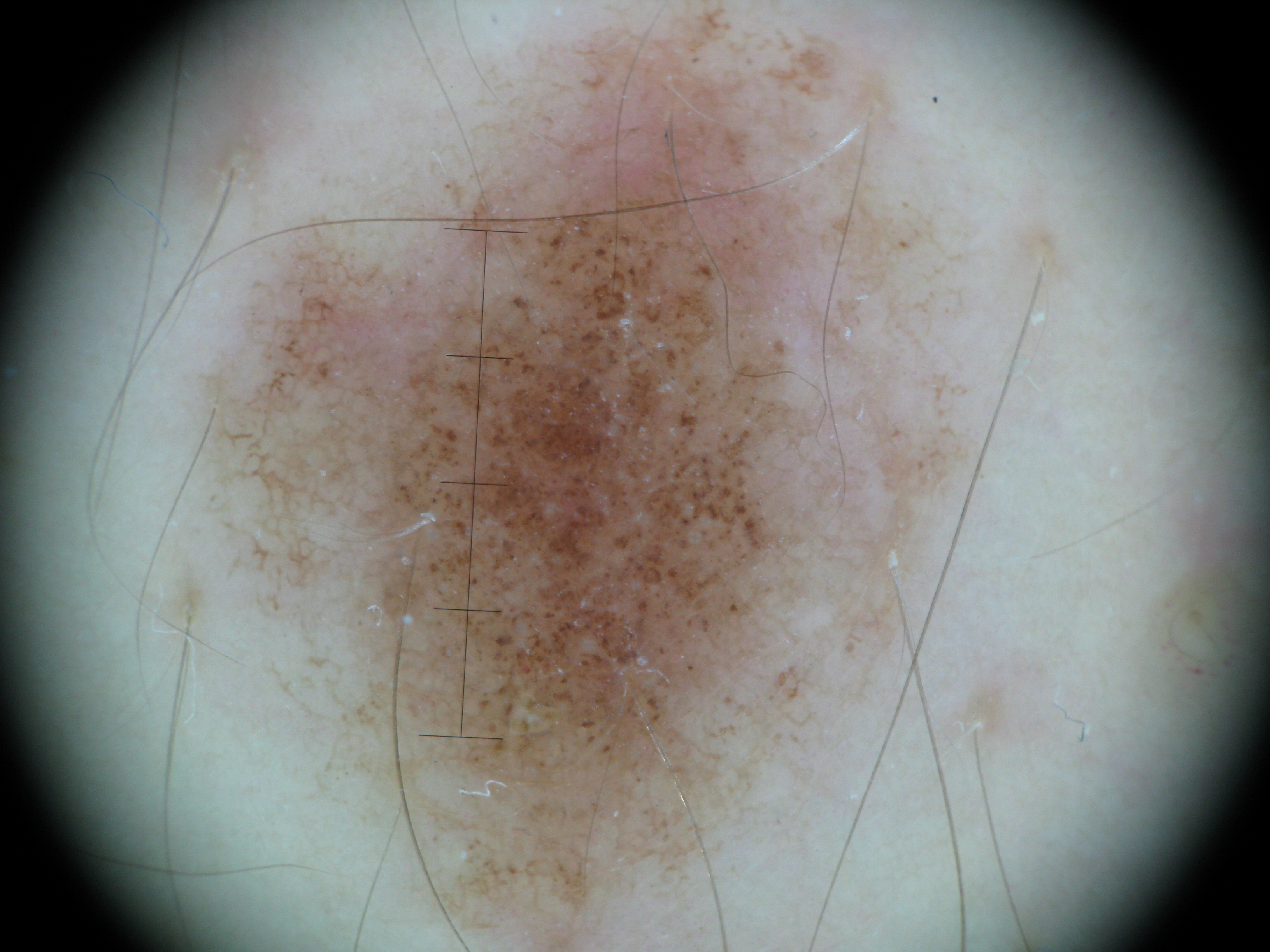Impression:
Classified as a dysplastic junctional nevus.